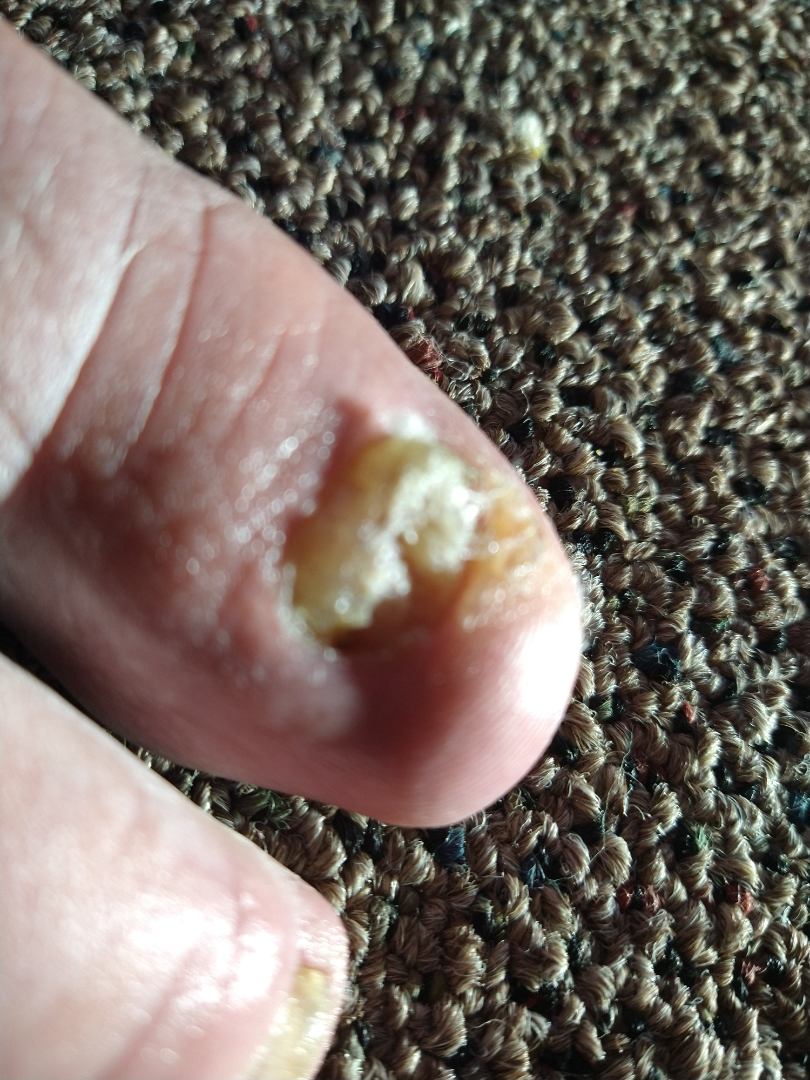The contributor is 50–59, male.
This image was taken at an angle.
Located on the top or side of the foot.
Favoring Onychomycosis; less probable is Verruca vulgaris; a remote consideration is Psoriasis; less likely is Nail dystrophy due to trauma.